Texture is reported as fluid-filled and raised or bumpy; located on the arm; symptoms reported: itching and bothersome appearance; the patient reports the condition has been present for one to four weeks; female contributor, age 18–29; Fitzpatrick III; an image taken at a distance; self-categorized by the patient as a rash.
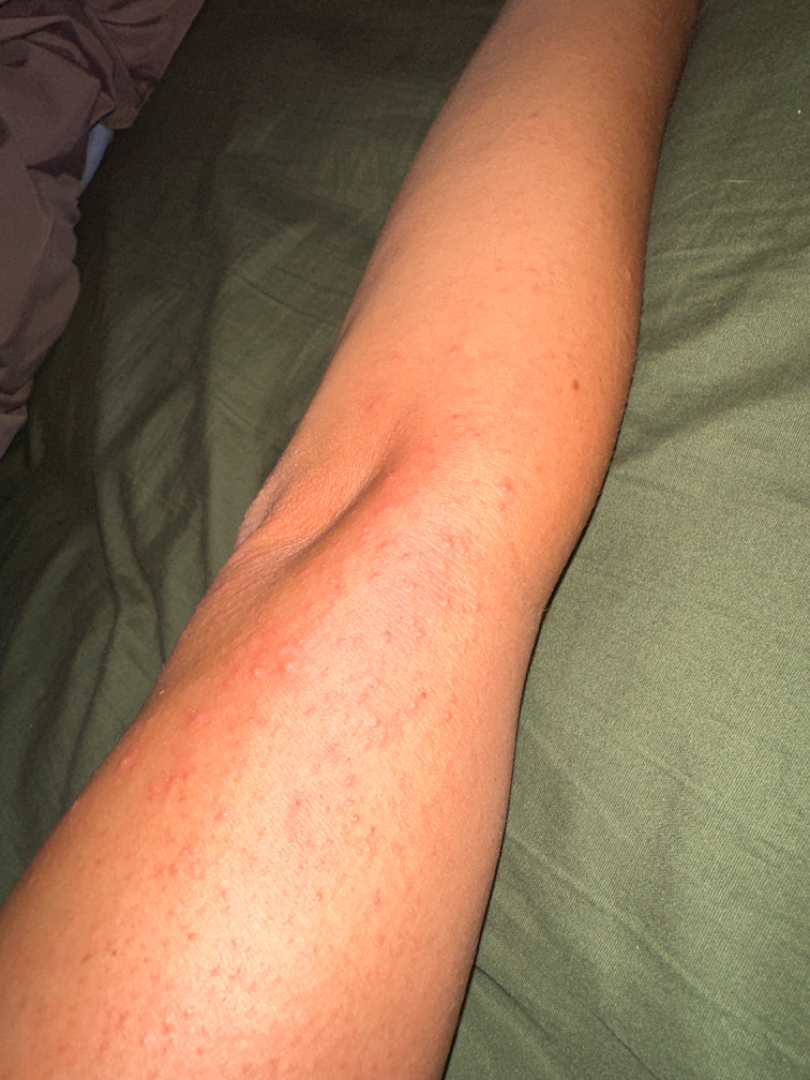On photographic review: in keeping with Acute dermatitis, NOS.